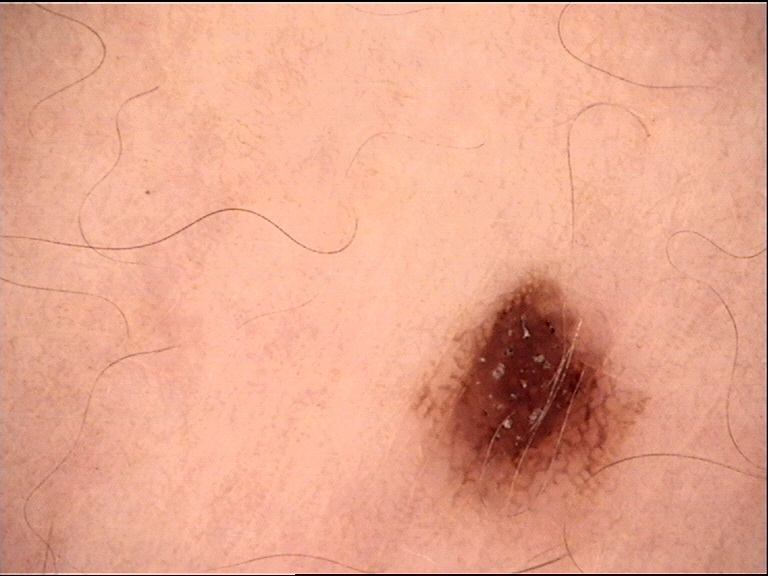A dermatoscopic image of a skin lesion. Diagnosed as a dysplastic junctional nevus.